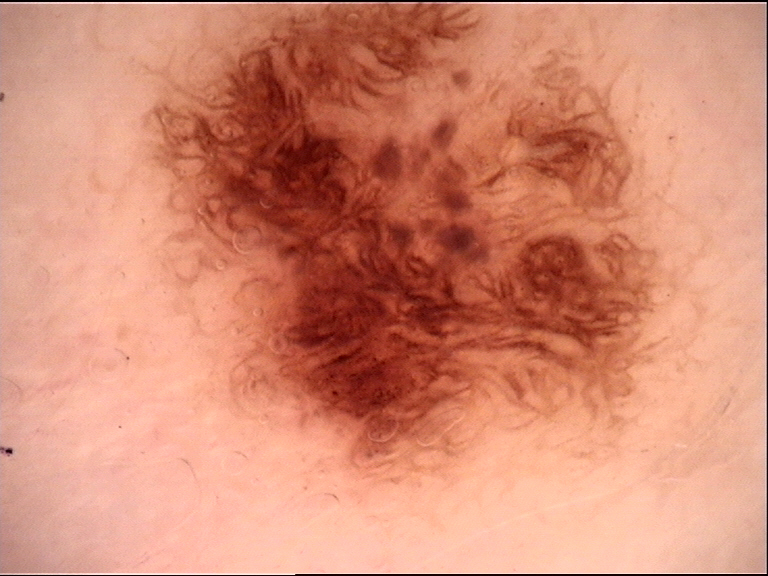Conclusion: Classified as a dysplastic junctional nevus.